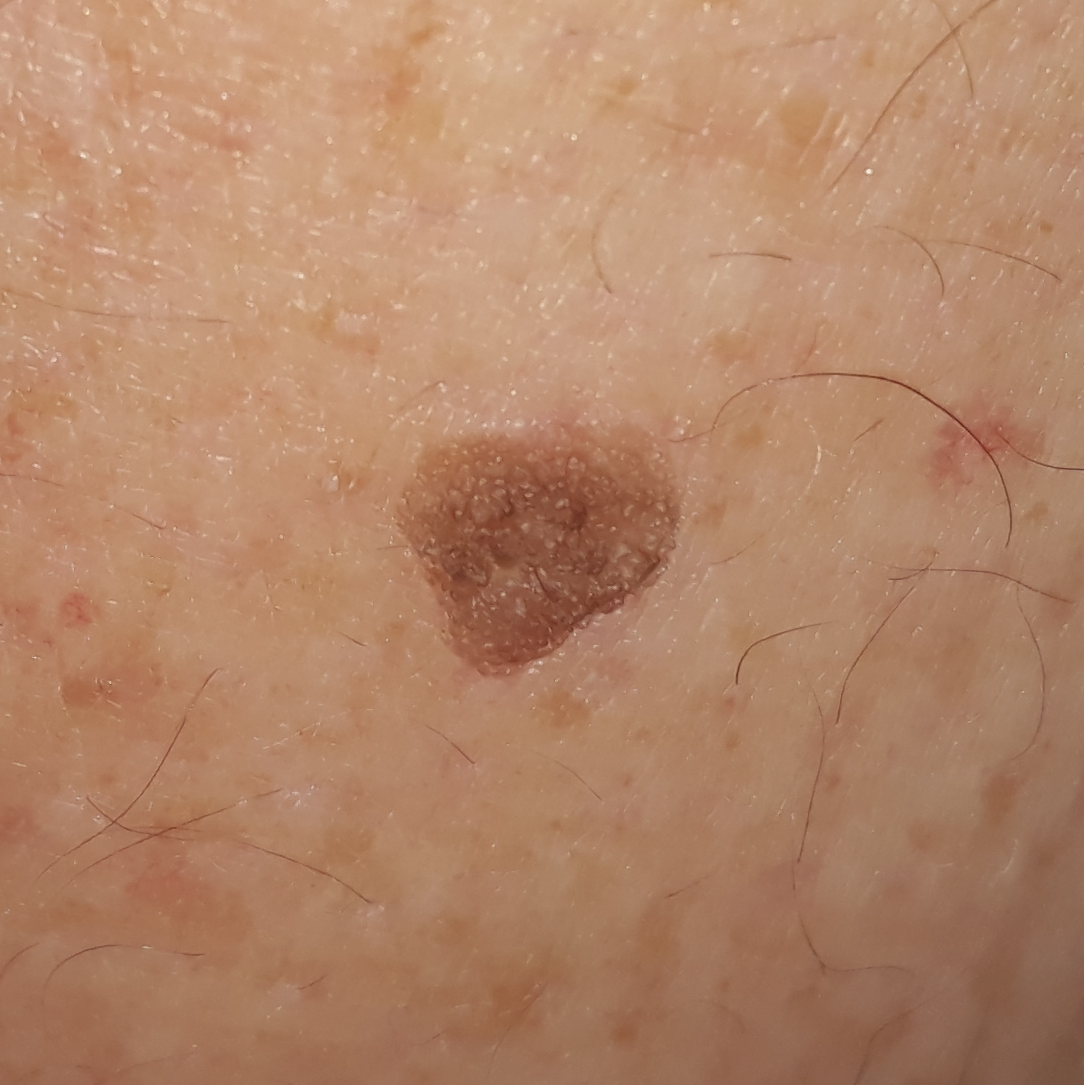A clinical photo of a skin lesion taken with a smartphone. A patient 55 years old. The lesion involves an arm. The patient reports no symptoms. Consistent with a seborrheic keratosis.